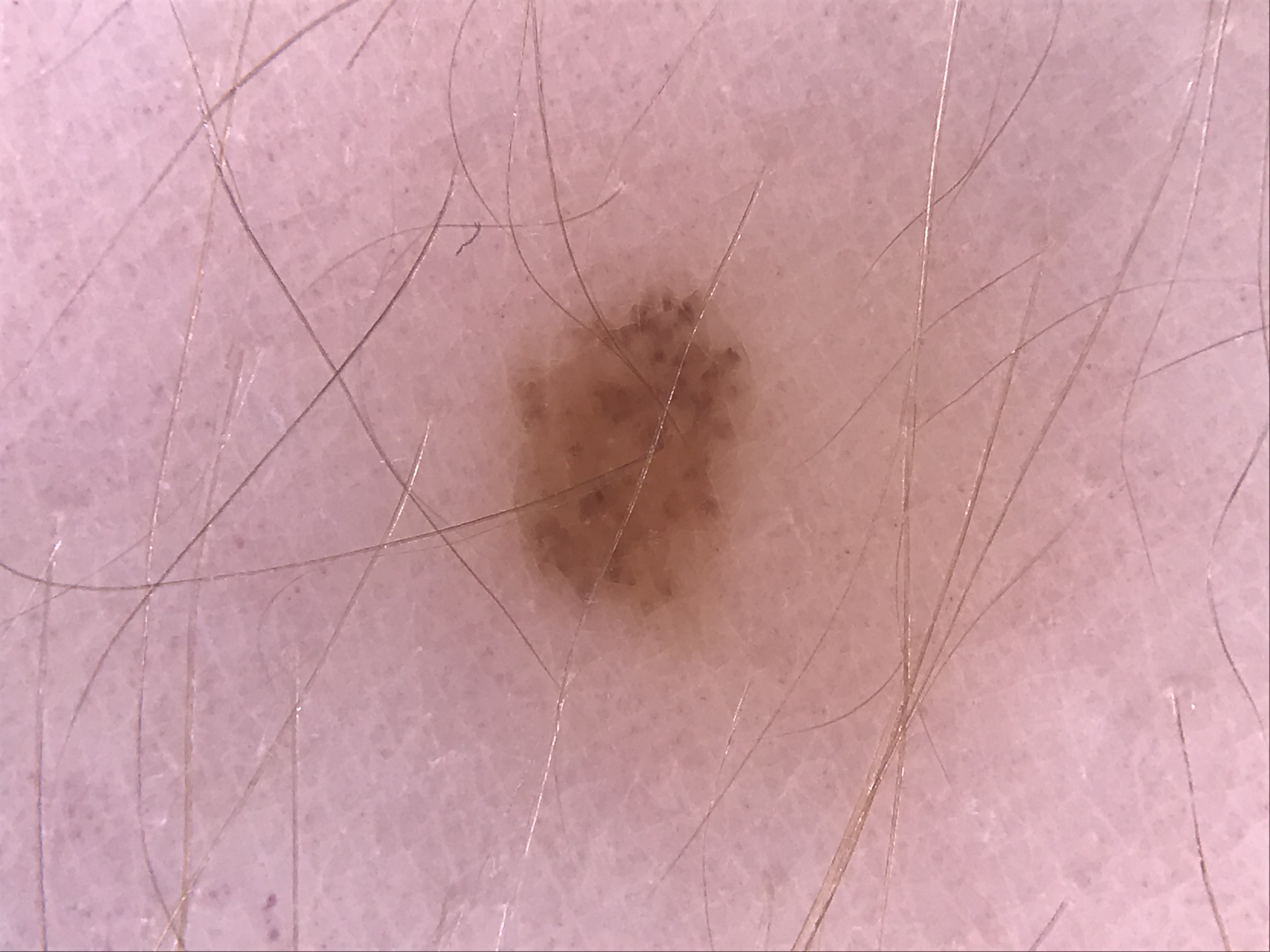{"image": "dermoscopy", "diagnosis": {"name": "dysplastic junctional nevus", "code": "jd", "malignancy": "benign", "super_class": "melanocytic", "confirmation": "expert consensus"}}